A dermoscopic close-up of a skin lesion:
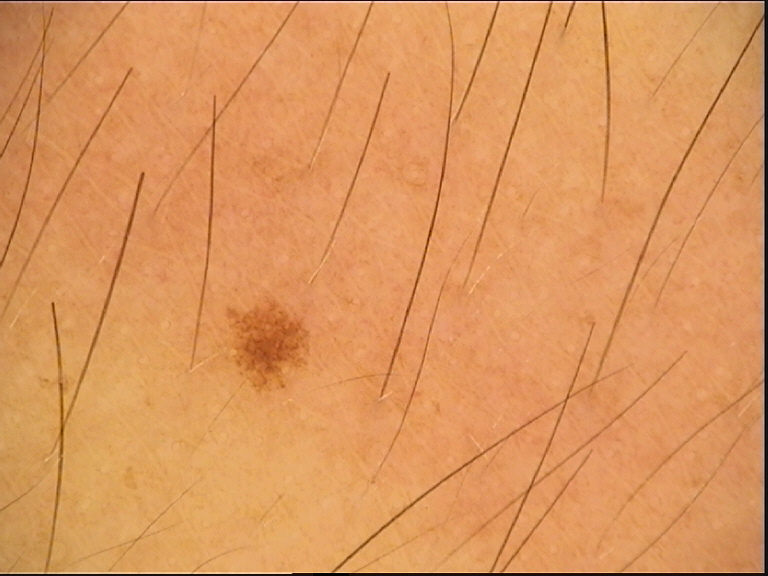Impression:
Diagnosed as a dysplastic junctional nevus.